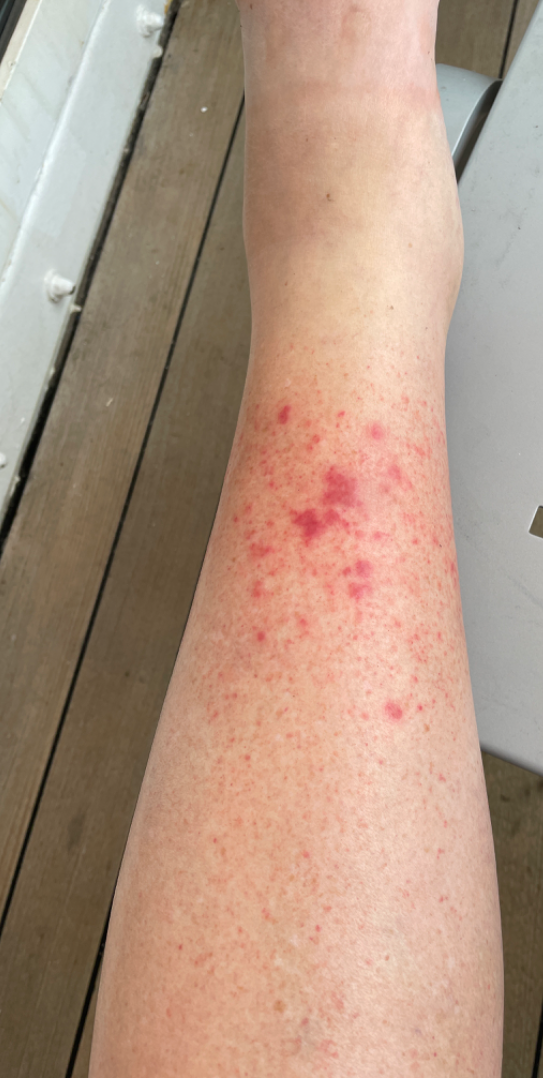Review:
On photographic review by a dermatologist: Leukocytoclastic Vasculitis (favored); Eczema (considered).